The patient is a female aged around 70; a dermoscopic close-up of a skin lesion — 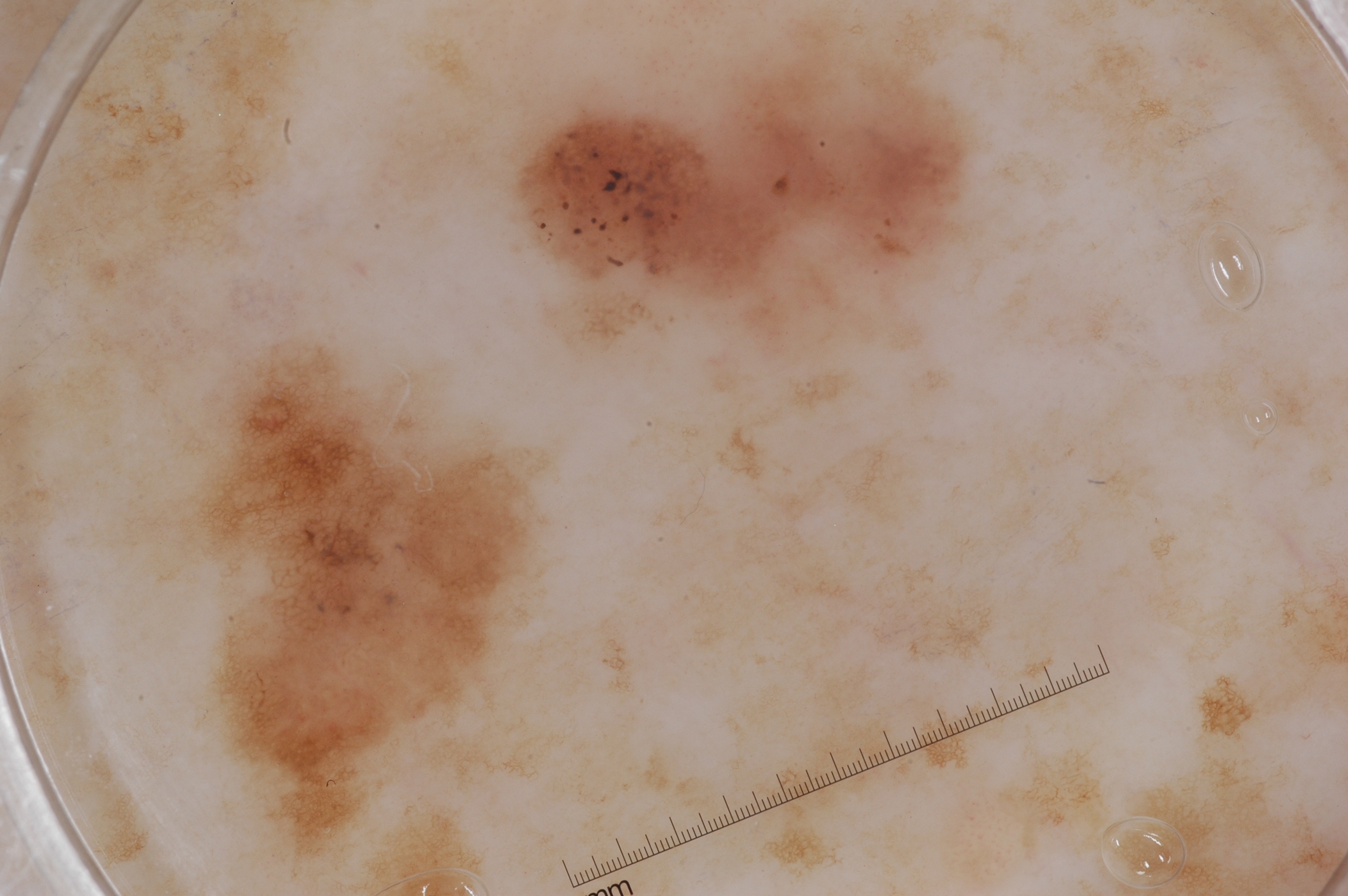  lesion_extent:
    approx_field_fraction_pct: 55
  lesion_location:
    bbox_xyxy:
      - 111
      - 5
      - 1085
      - 887
  dermoscopic_features:
    present:
      - pigment network
    absent:
      - streaks
      - milia-like cysts
      - negative network
  diagnosis:
    name: melanoma
    malignancy: malignant
    lineage: melanocytic
    provenance: histopathology